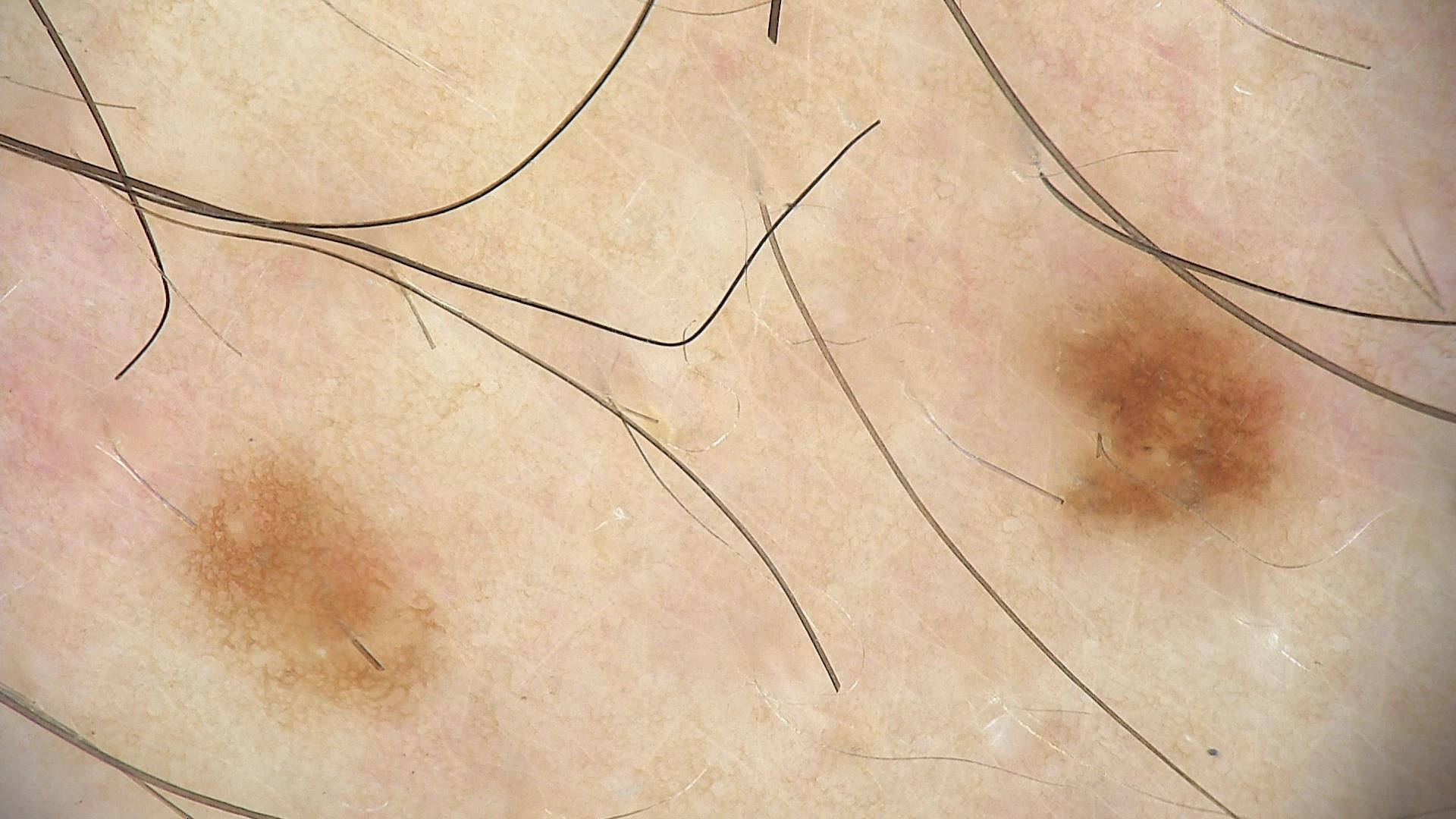{"diagnosis": {"name": "dysplastic junctional nevus", "code": "jd", "malignancy": "benign", "super_class": "melanocytic", "confirmation": "expert consensus"}}